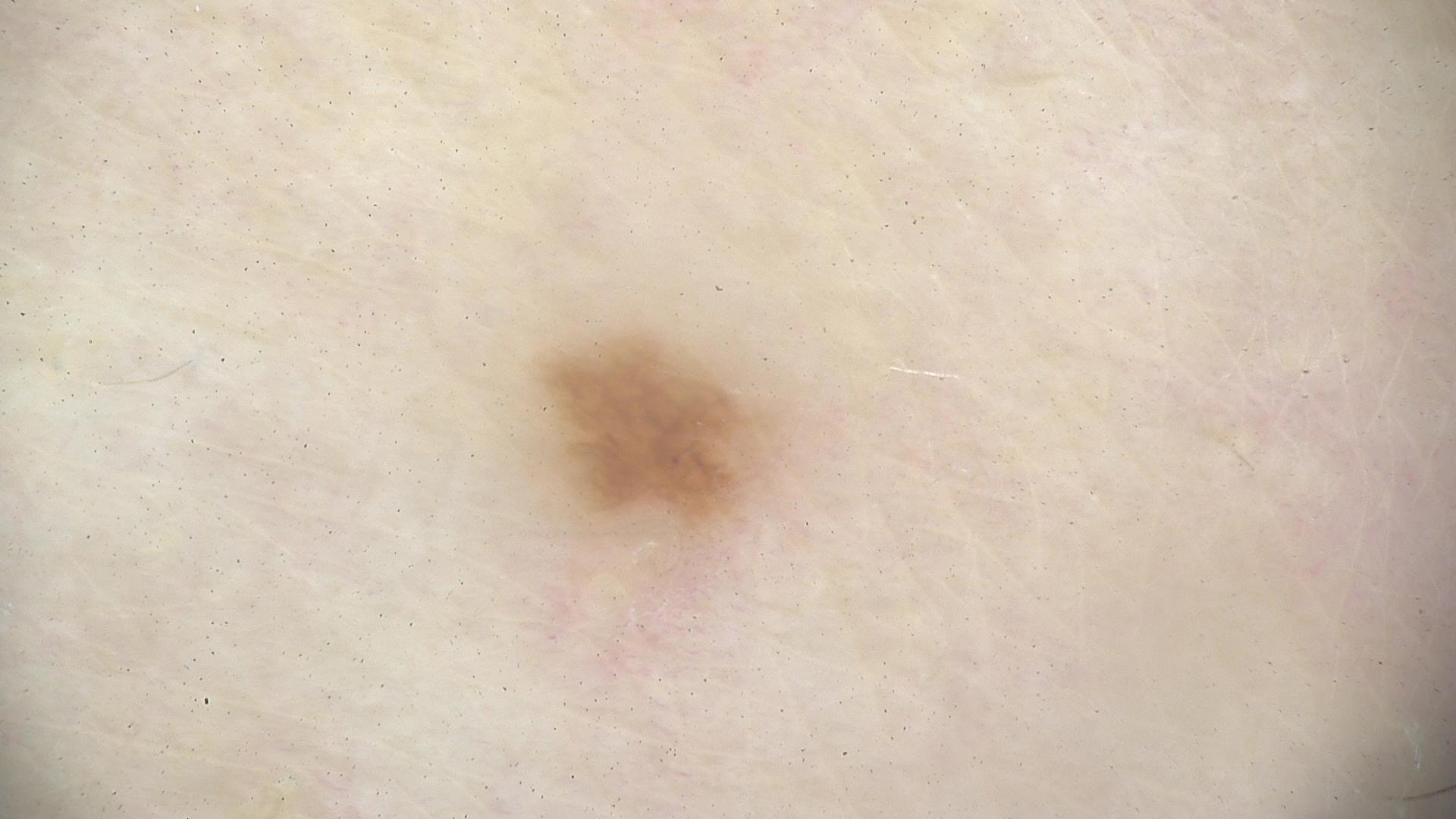image type: dermoscopy | diagnostic label: dysplastic junctional nevus (expert consensus).